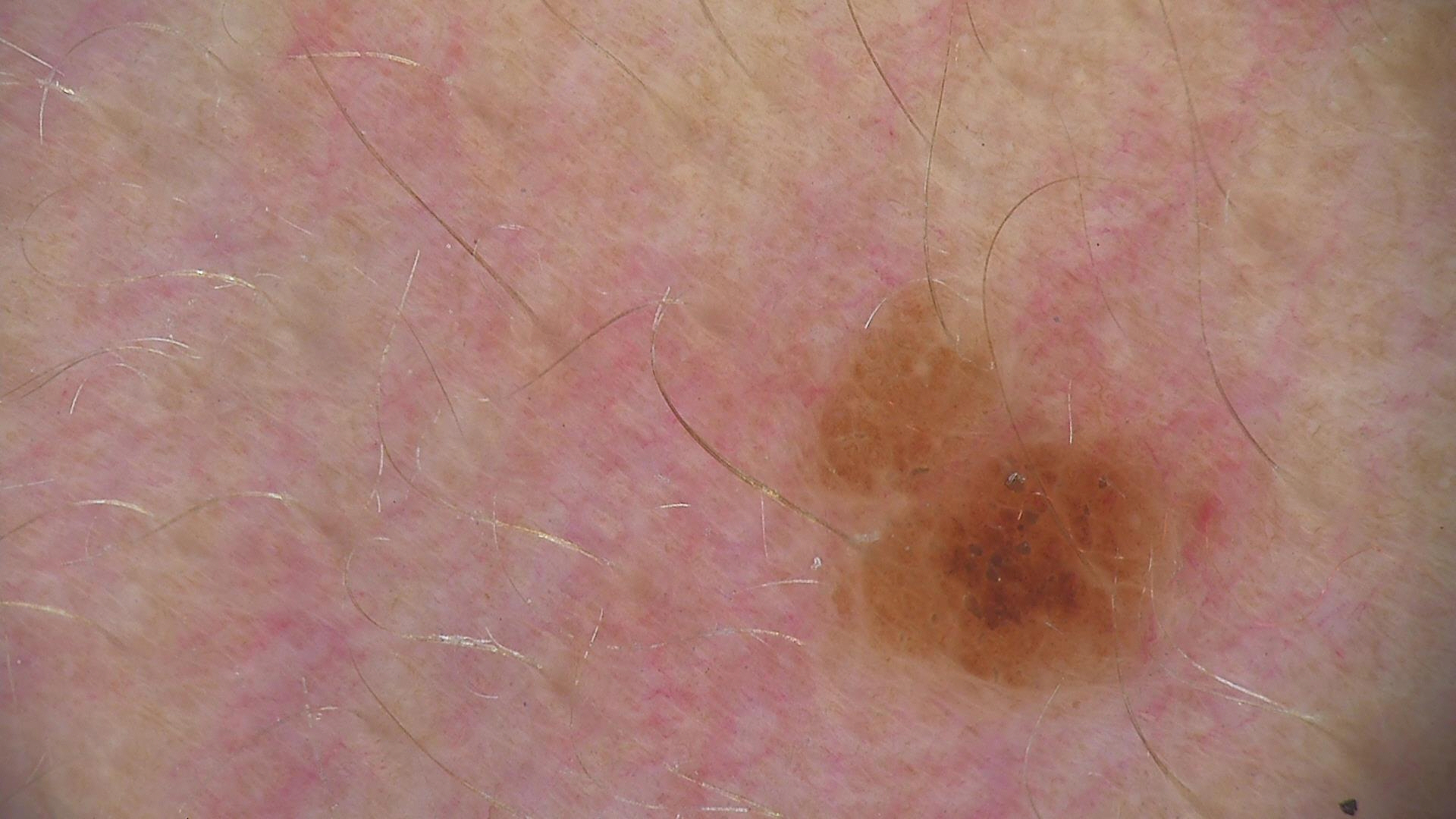A dermoscopic photograph of a skin lesion. Classified as a benign lesion — a dysplastic junctional nevus.